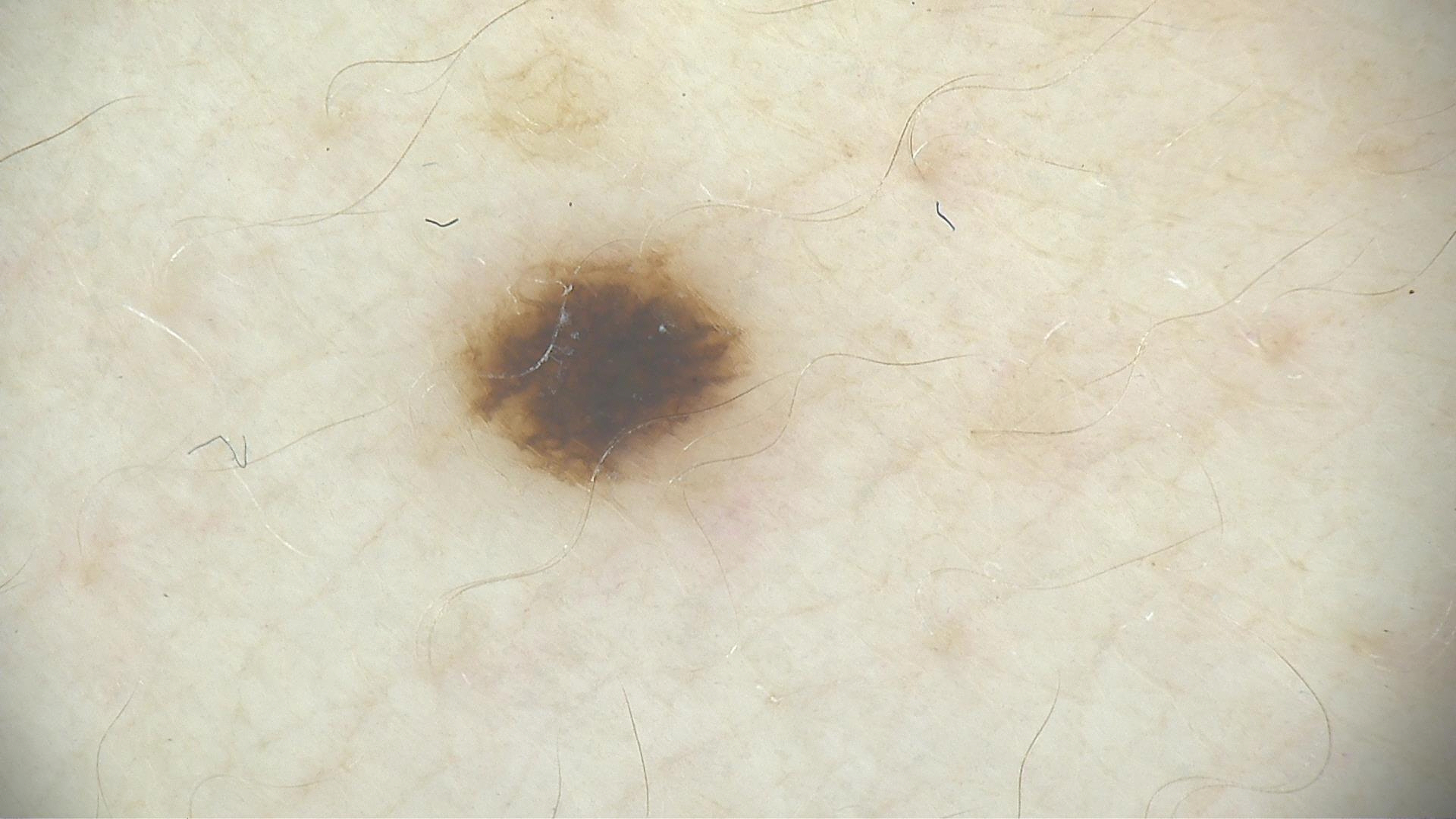imaging = dermatoscopy | diagnostic label = dysplastic junctional nevus (expert consensus).